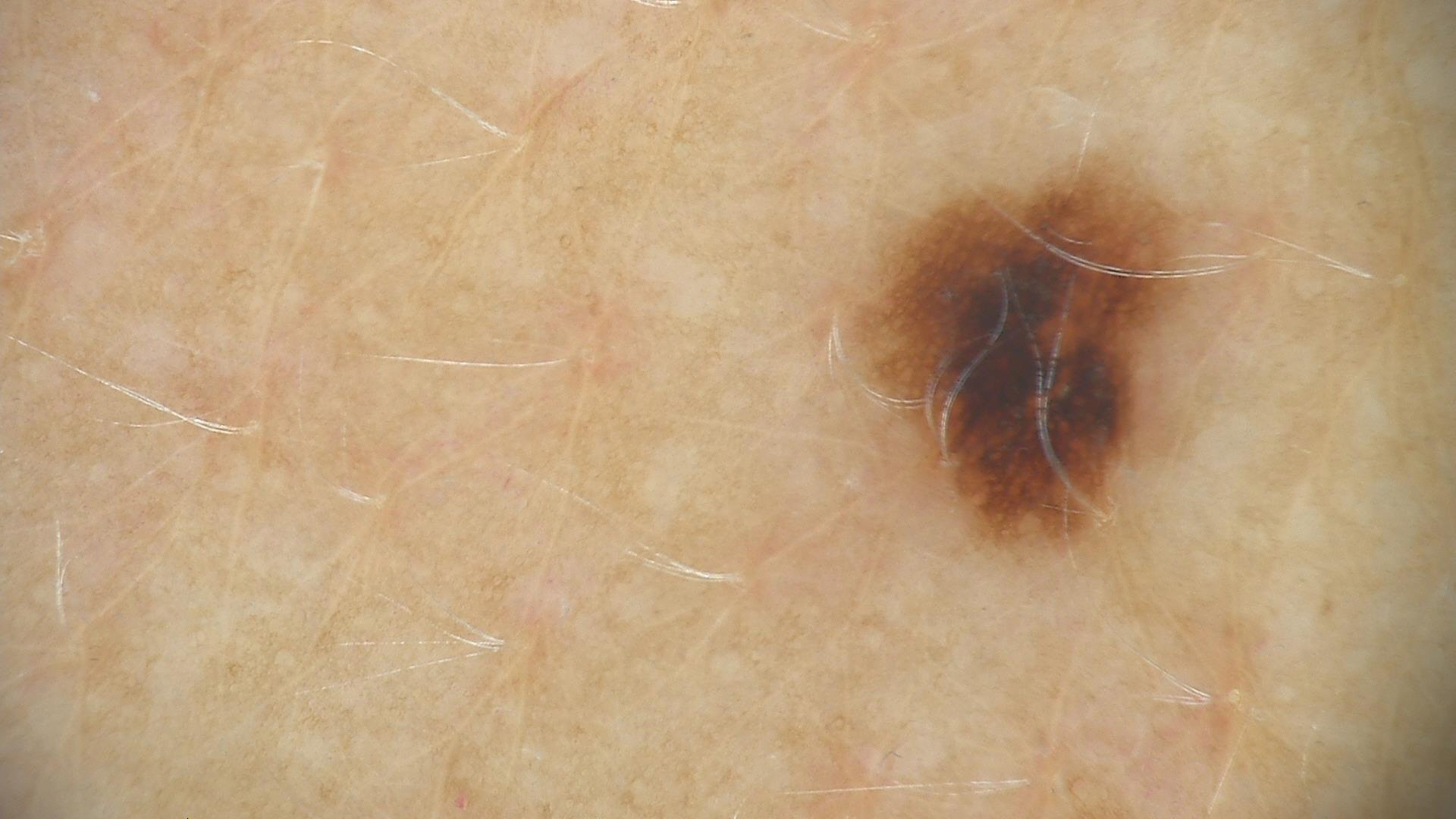Q: What is this lesion?
A: dysplastic junctional nevus (expert consensus)